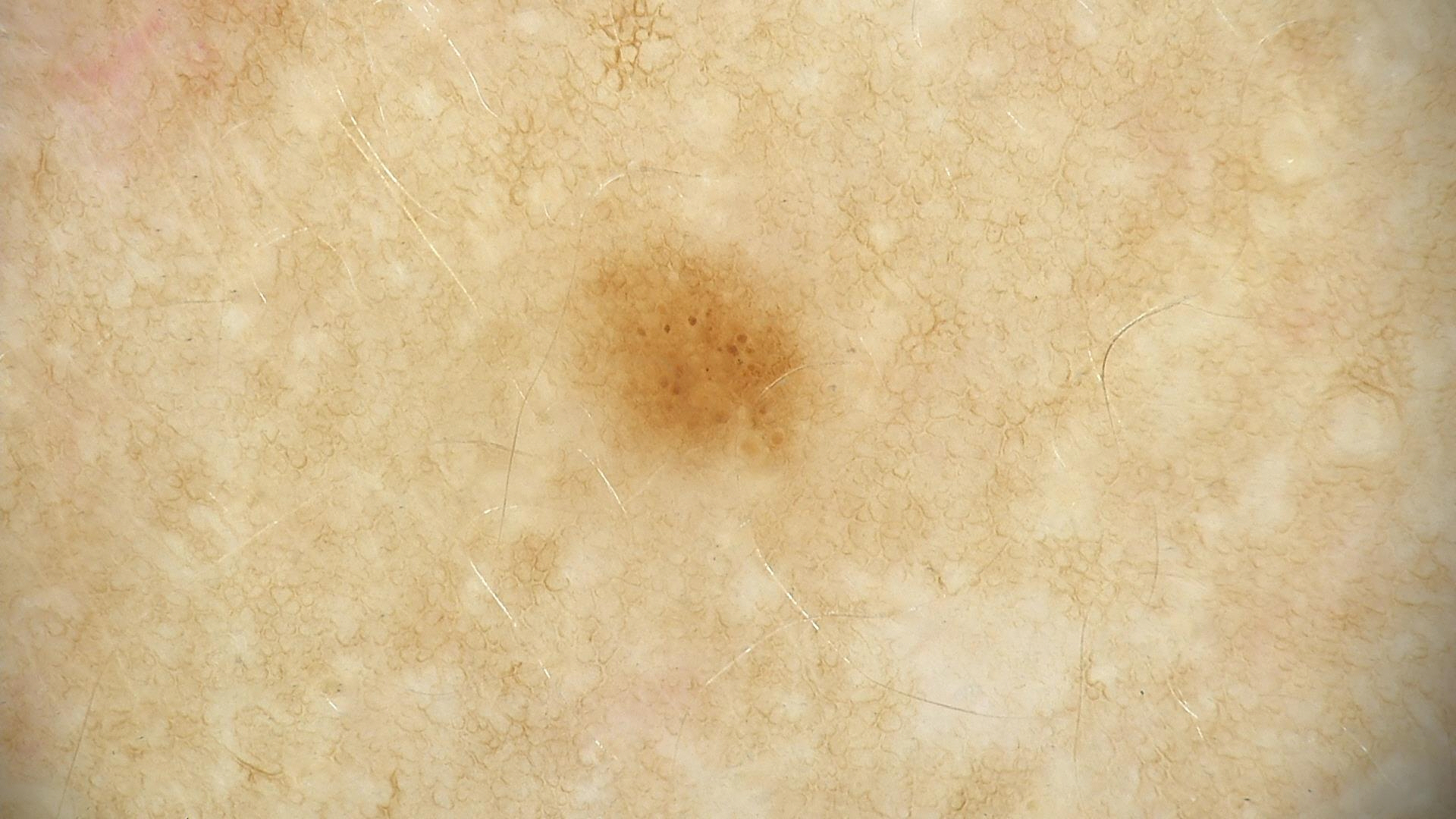label = dysplastic junctional nevus (expert consensus).